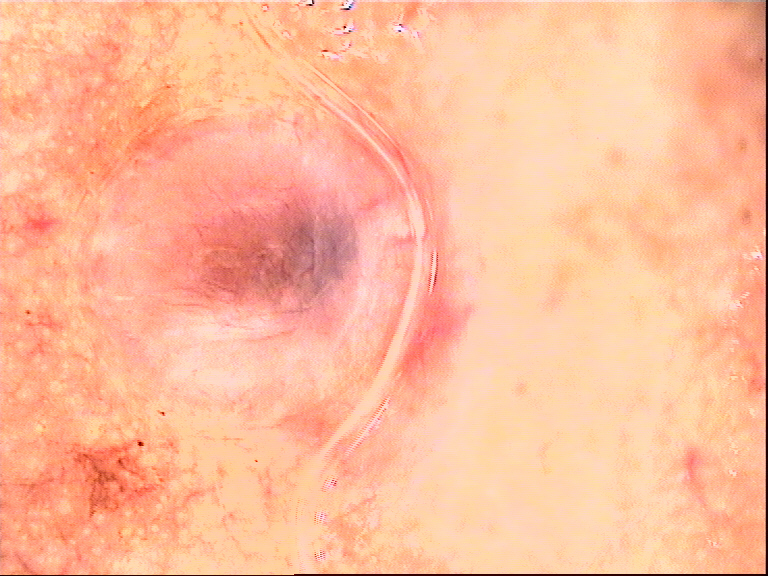image type: dermoscopy
lesion type: banal
diagnosis: dermal nevus (expert consensus)